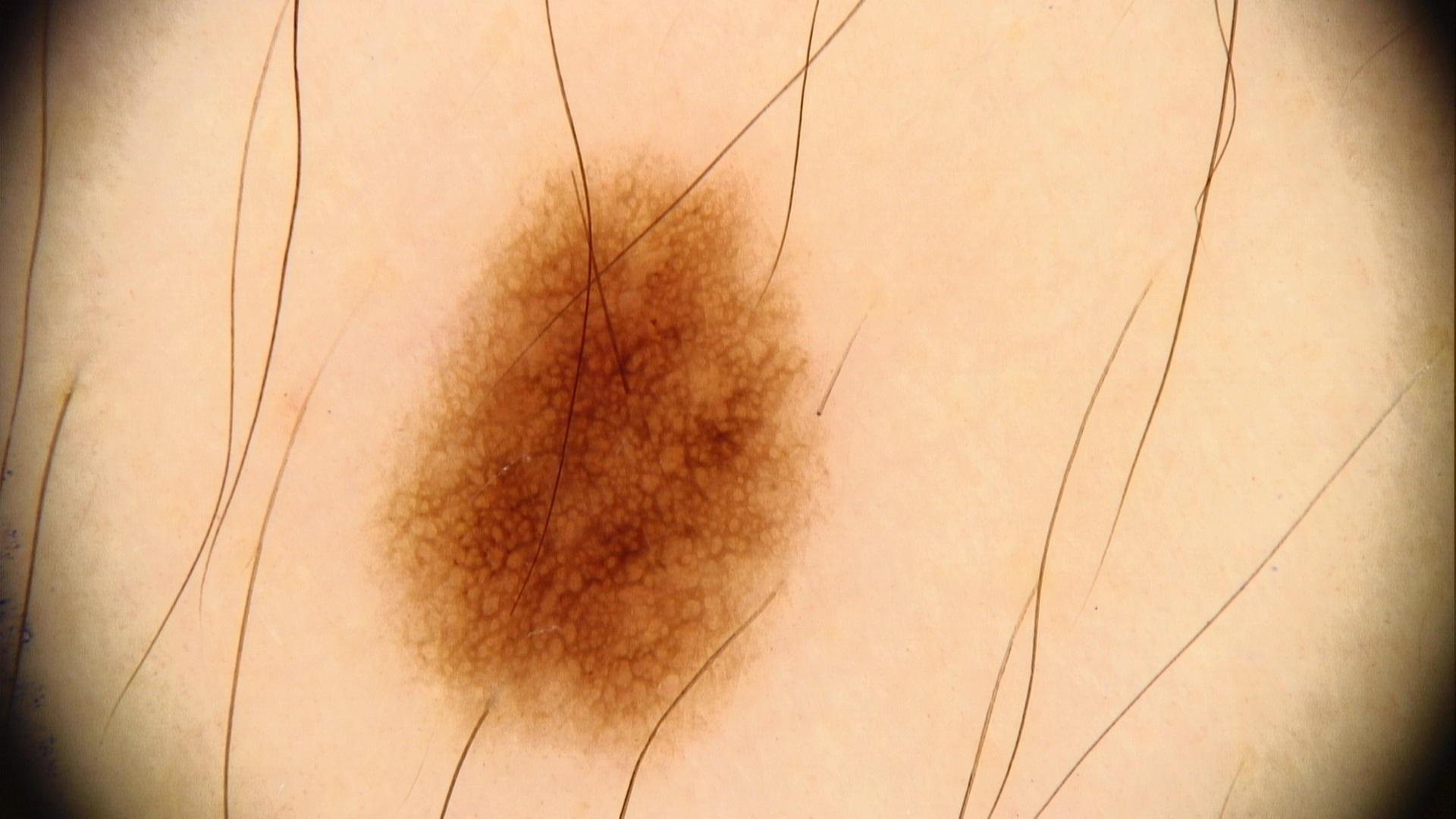Expert review favored a nevus.